Located on the leg and arm. The subject is a female aged 30–39. The photograph is a close-up of the affected area: 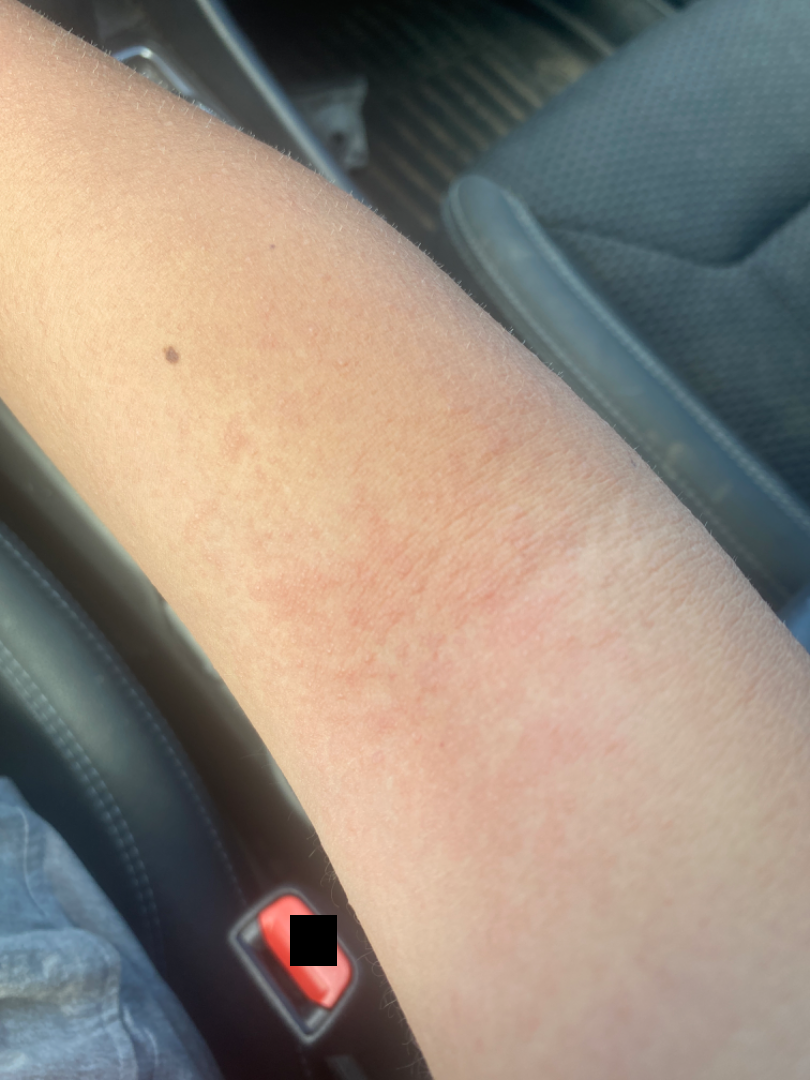Impression:
On remote dermatologist review, Eczema (most likely); Viral Exanthem (possible); Allergic Contact Dermatitis (possible).